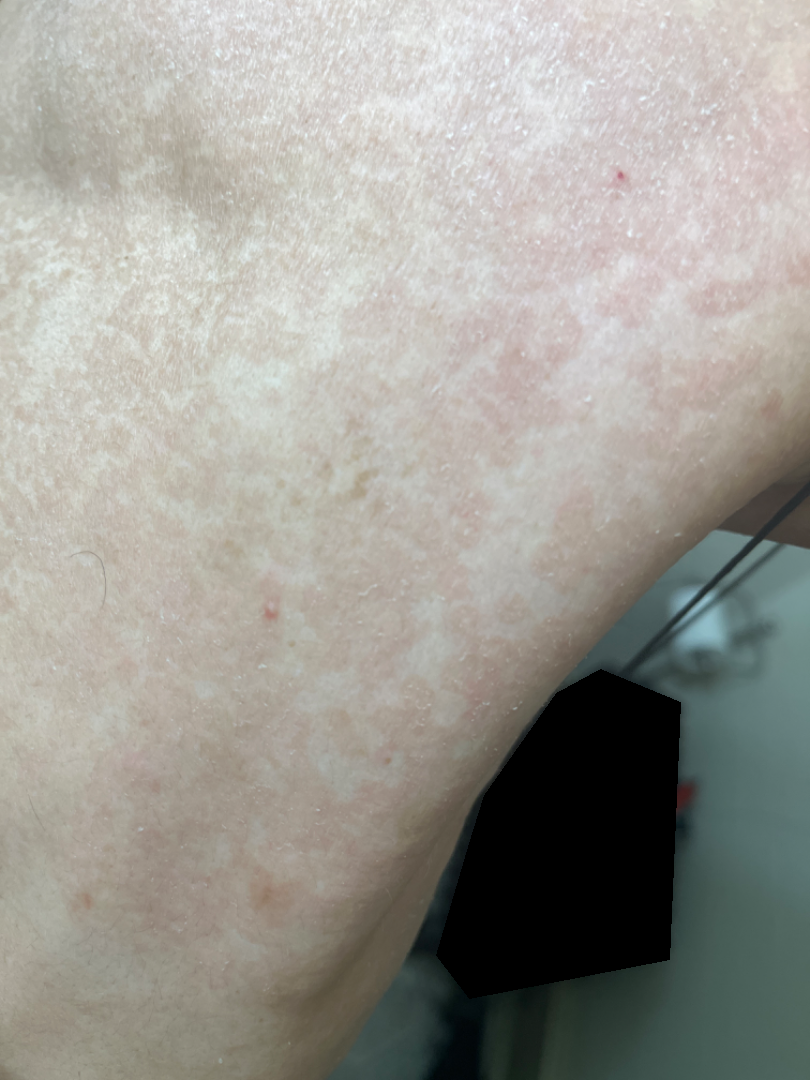Q: Constitutional symptoms?
A: fatigue
Q: What symptoms does the patient report?
A: bothersome appearance and itching
Q: Image view?
A: close-up
Q: Where on the body?
A: back of the torso and front of the torso
Q: Duration?
A: more than one year
Q: What conditions are considered?
A: most consistent with Tinea Versicolor; less likely is Psoriasis; lower on the differential is Pityriasis rubra pilaris; a remote consideration is Tinea